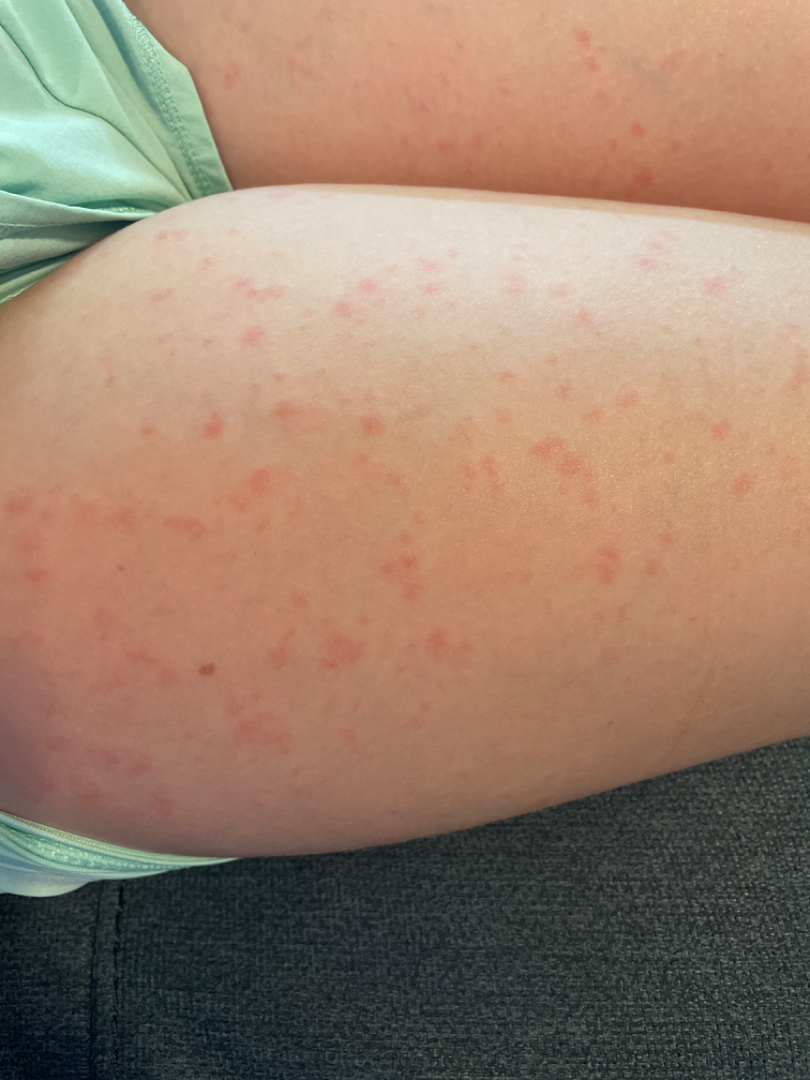{"patient": "female, age 18–29", "symptoms": "none reported", "body_site": "leg", "duration": "about one day", "texture": "flat", "patient_category": "a rash", "shot_type": "close-up", "differential": {"leading": ["Viral Exanthem"], "considered": ["Drug Rash"], "unlikely": ["Urticaria", "Eczema"]}}